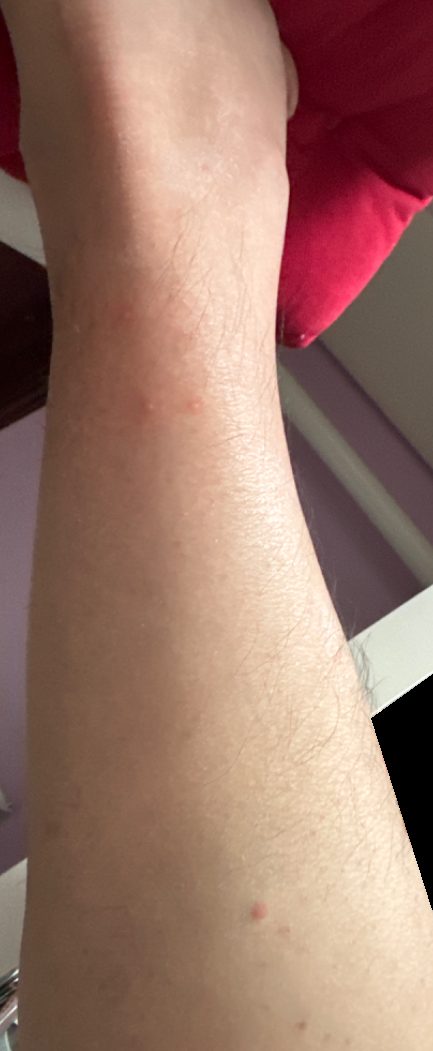Q: How was the photo taken?
A: at a distance
Q: Patient demographics?
A: male
Q: Where on the body?
A: leg
Q: What is the differential diagnosis?
A: the reviewer's impression was Insect Bite